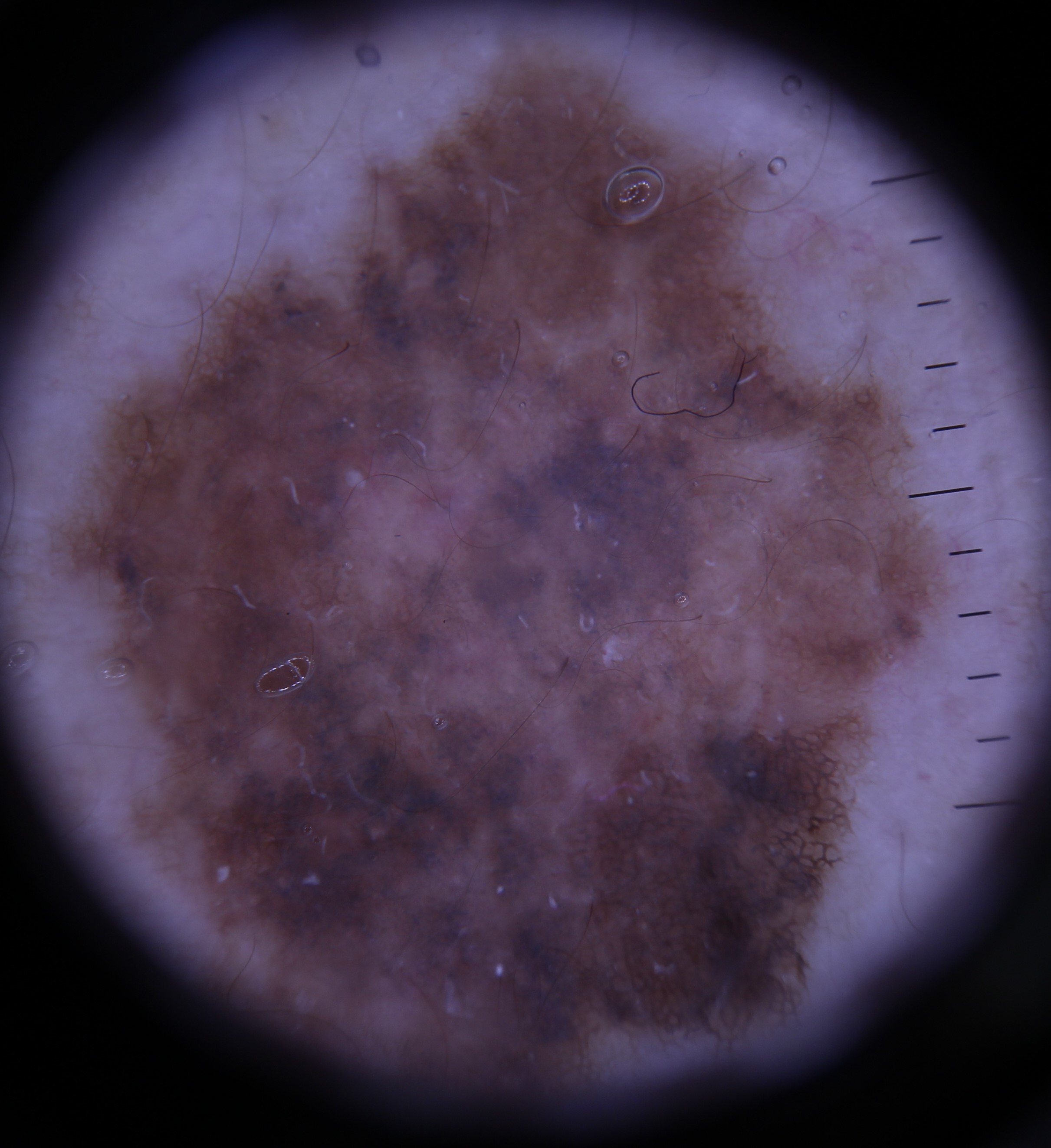Conclusion:
Biopsy-confirmed as a melanoma.